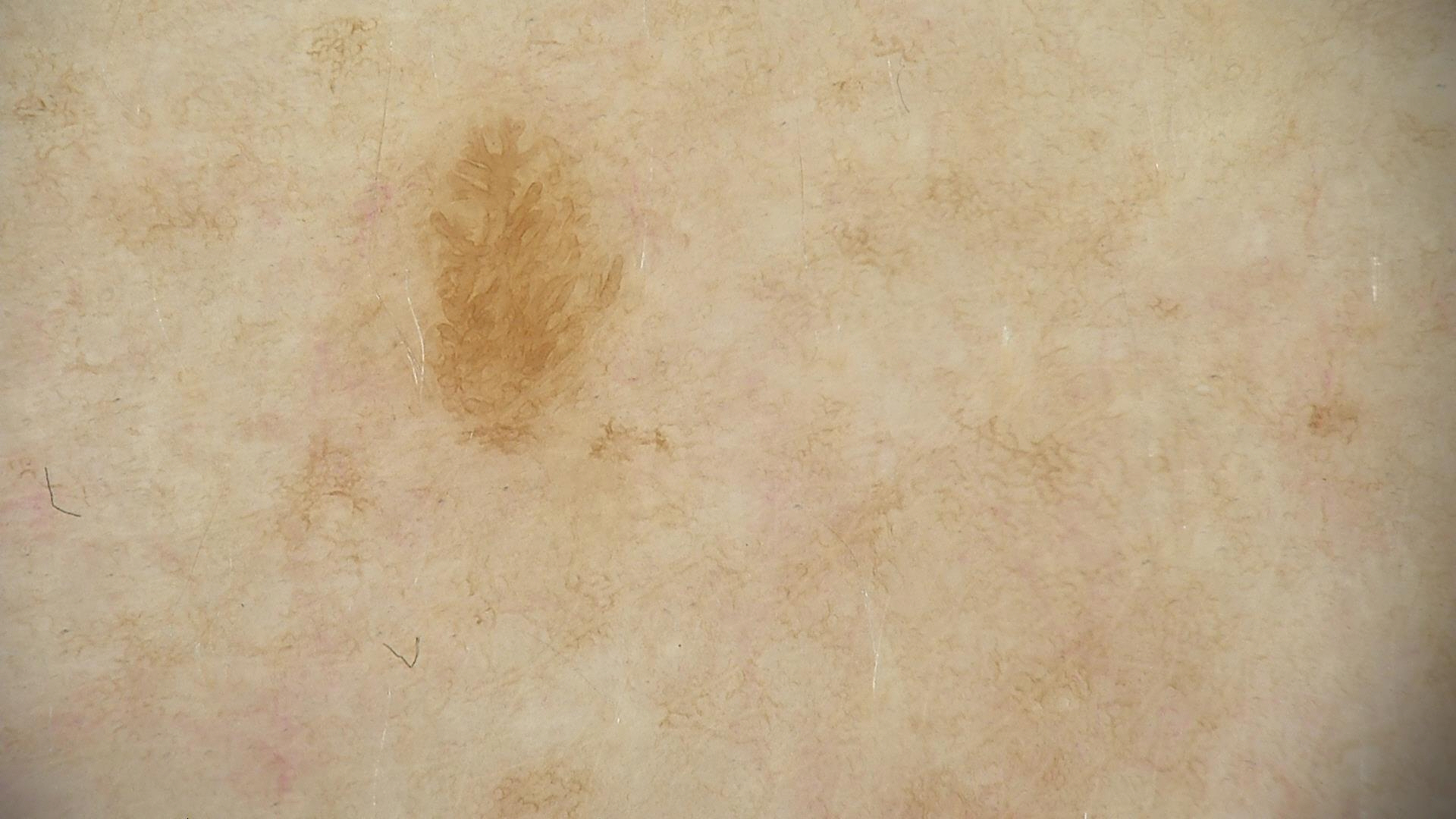{
  "image": "dermoscopy",
  "lesion_type": {
    "main_class": "keratinocytic"
  },
  "diagnosis": {
    "name": "seborrheic keratosis",
    "code": "sk",
    "malignancy": "benign",
    "super_class": "non-melanocytic",
    "confirmation": "expert consensus"
  }
}